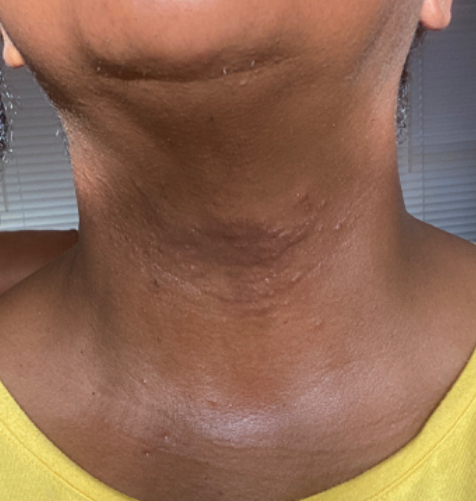Q: What is the dermatologist's impression?
A: the differential, in no particular order, includes Allergic Contact Dermatitis and Cutaneous sarcoidosis; less likely is Eczema; a remote consideration is Drug Rash; less probable is Lichenoid myxedema